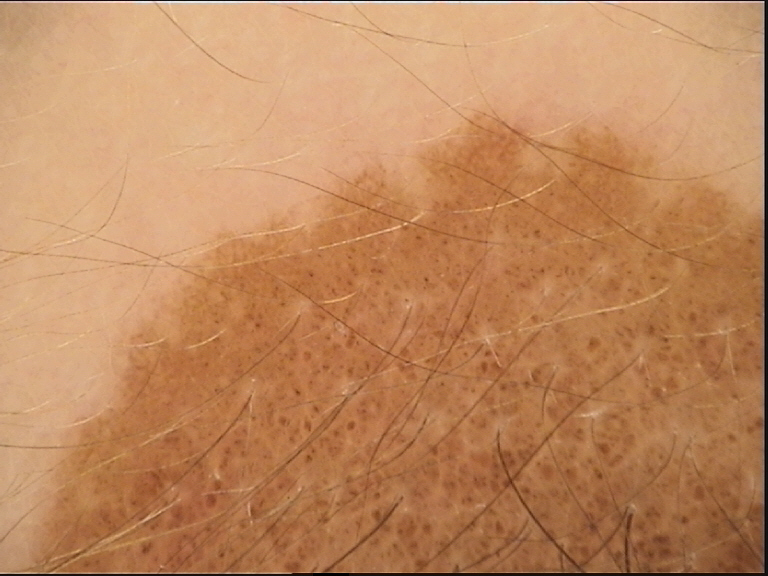image type: dermoscopy, classification: banal, label: congenital compound nevus (expert consensus).